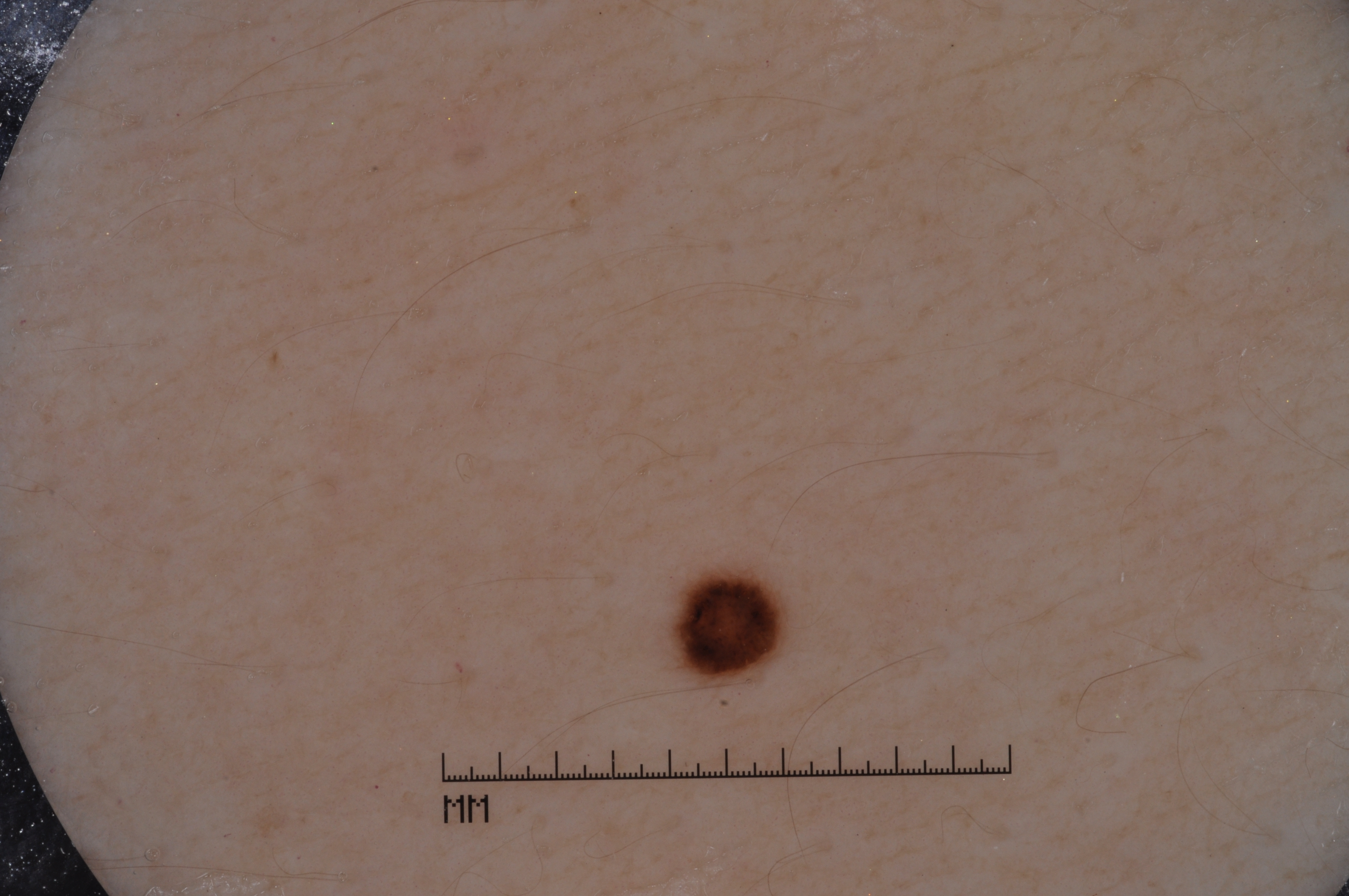modality=dermoscopy of a skin lesion
subject=female, aged approximately 35
bounding box=[669,570,789,690]
extent=~1% of the field
absent dermoscopic findings=streaks, negative network, milia-like cysts, and pigment network
assessment=a melanocytic nevus